A dermoscopic image of a skin lesion.
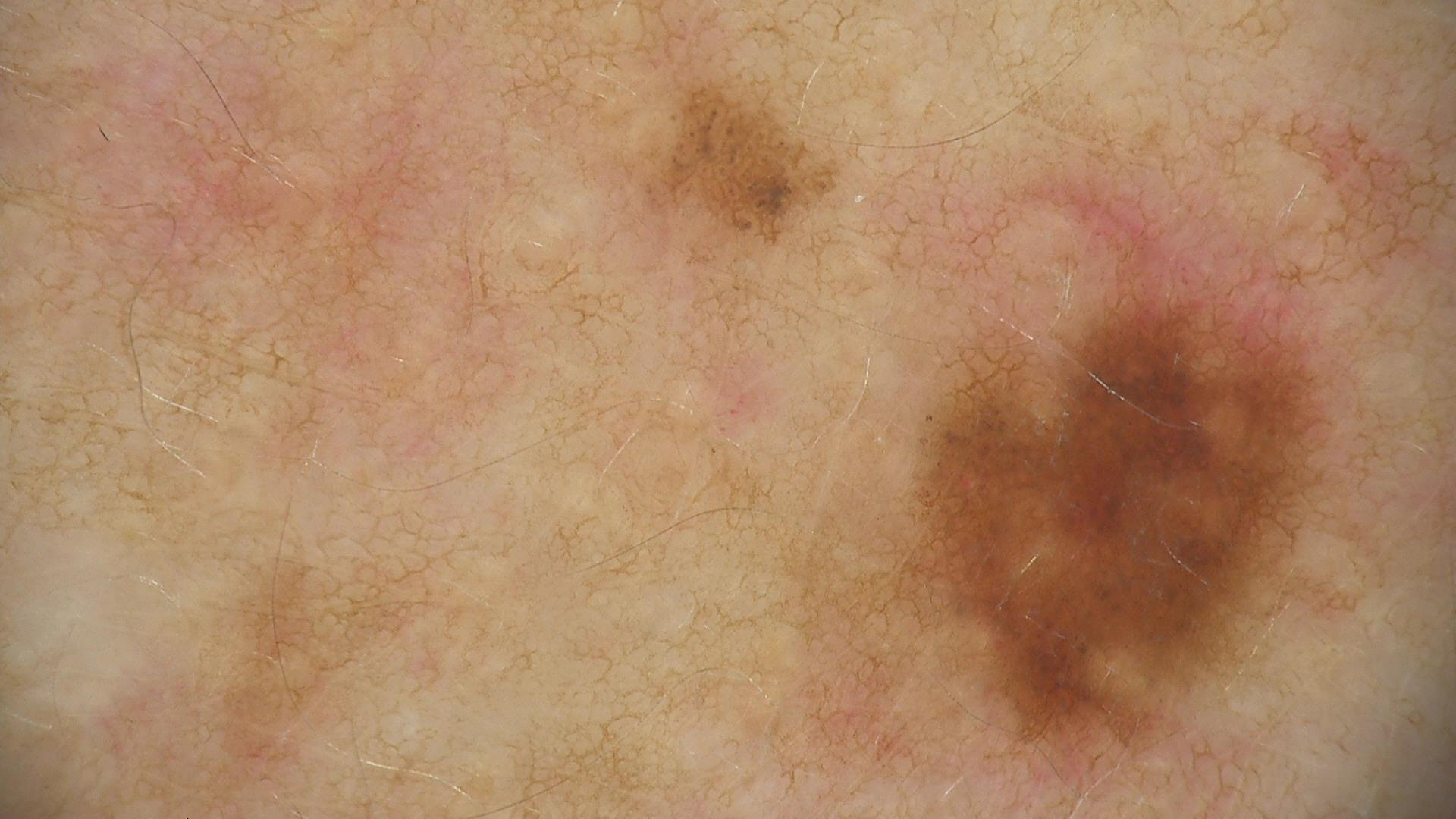Labeled as a dysplastic junctional nevus.